A dermoscopic close-up of a skin lesion:
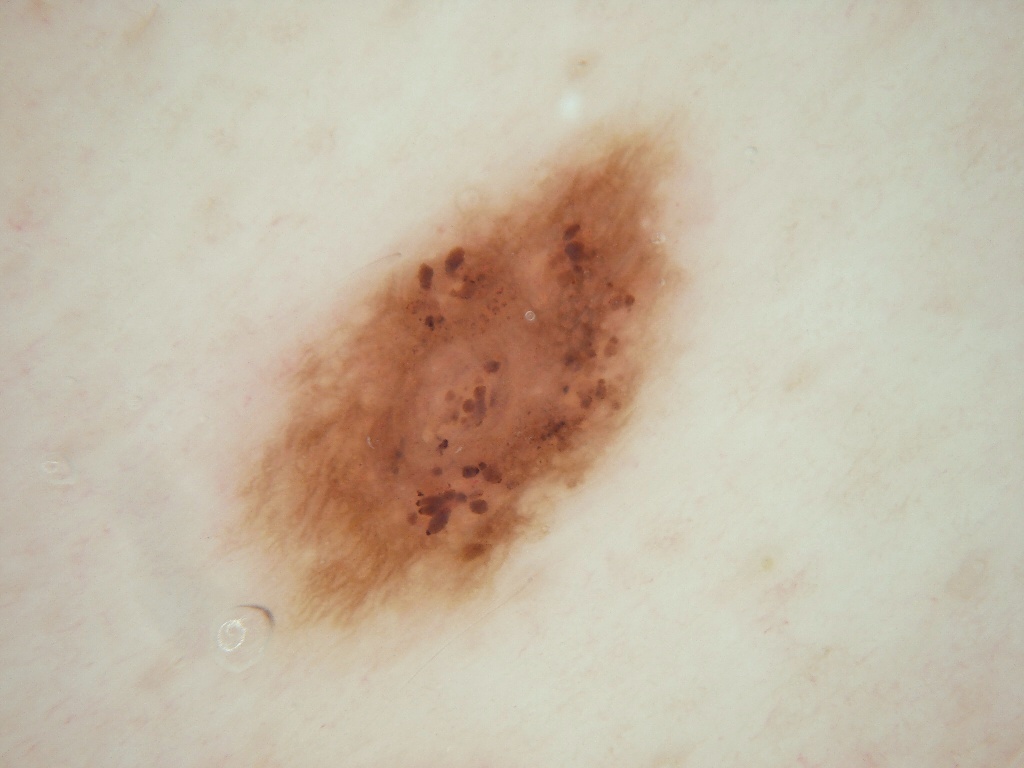location=<box>217, 116, 692, 649</box> | dermoscopic features=pigment network and globules; absent: milia-like cysts, streaks, and negative network | impression=a melanocytic nevus.